Located on the leg; symptoms reported: burning and enlargement; no associated systemic symptoms reported; FST III; the patient notes the condition has been present for less than one week; the photo was captured at an angle:
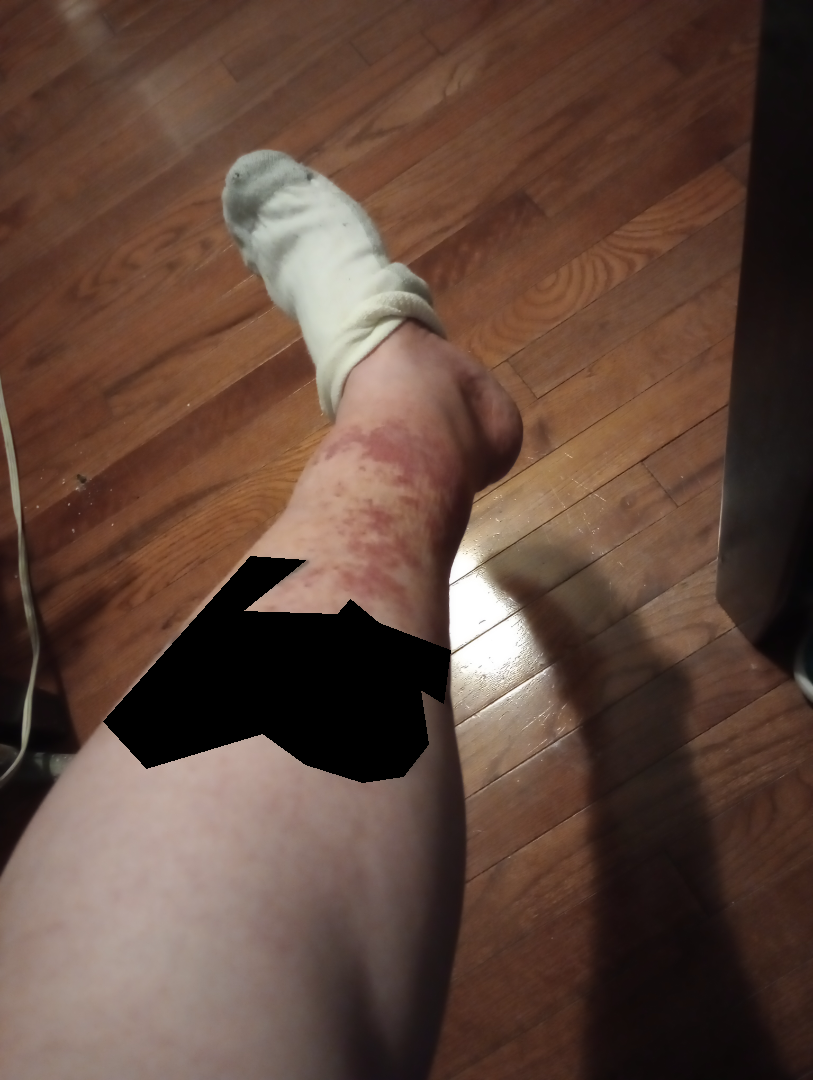Assessment:
On photographic review: the differential is split between Photodermatitis, Eczema and Irritant Contact Dermatitis.